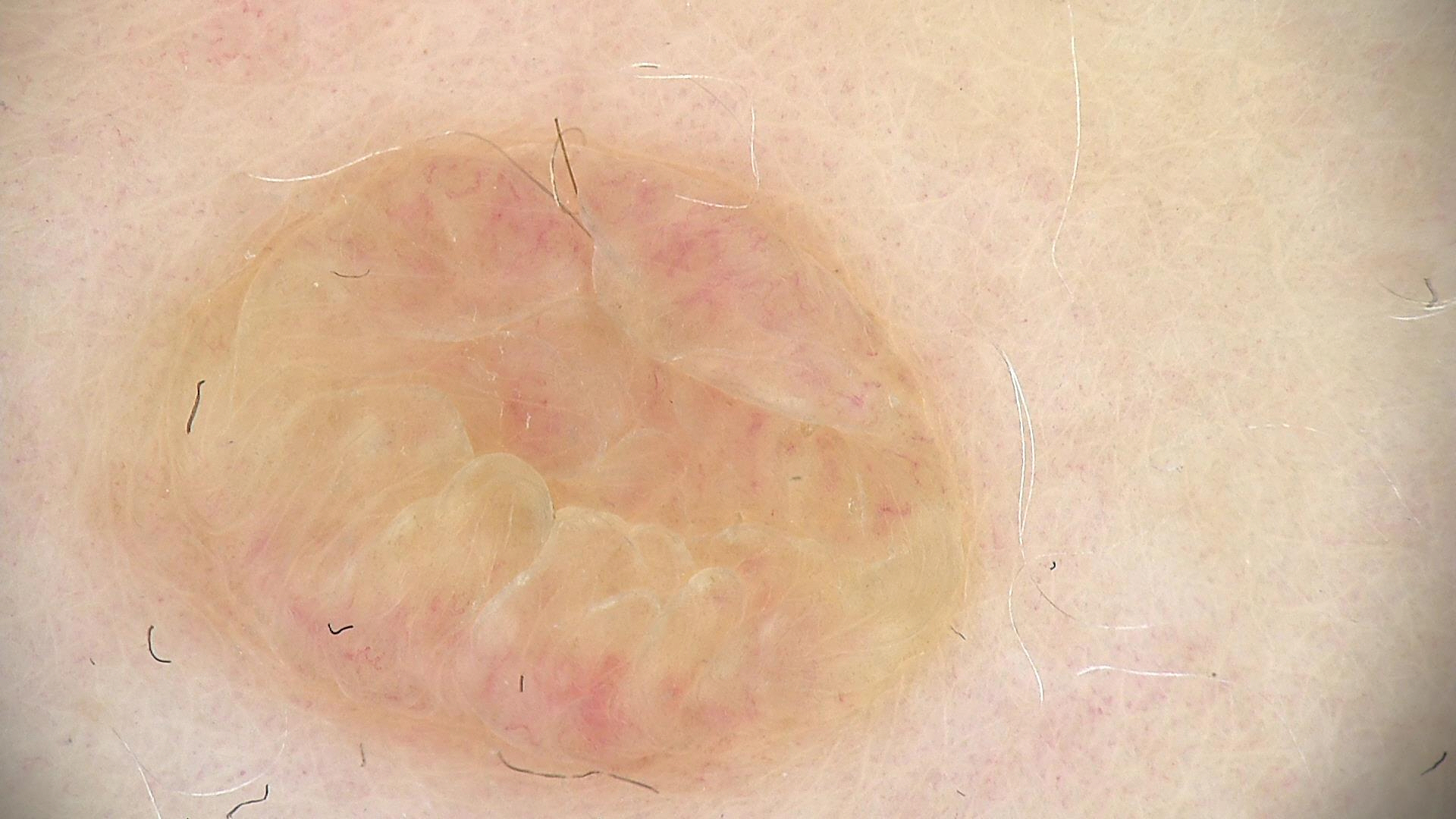Impression:
Classified as a dermal nevus.